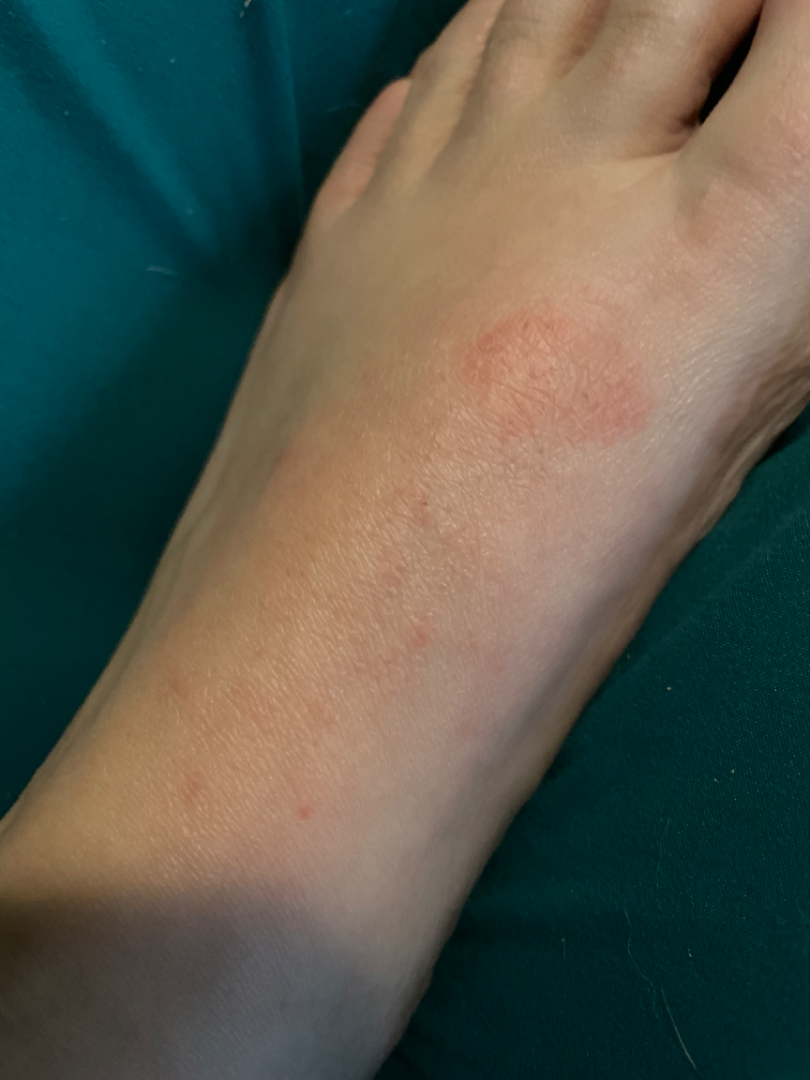differential = reviewed remotely by one dermatologist: the impression was split between Lichen Simplex Chronicus, Allergic Contact Dermatitis and Irritant Contact Dermatitis